The patient was assessed as Fitzpatrick phototype II; a dermoscopic photograph of a skin lesion; a female subject aged approximately 65: 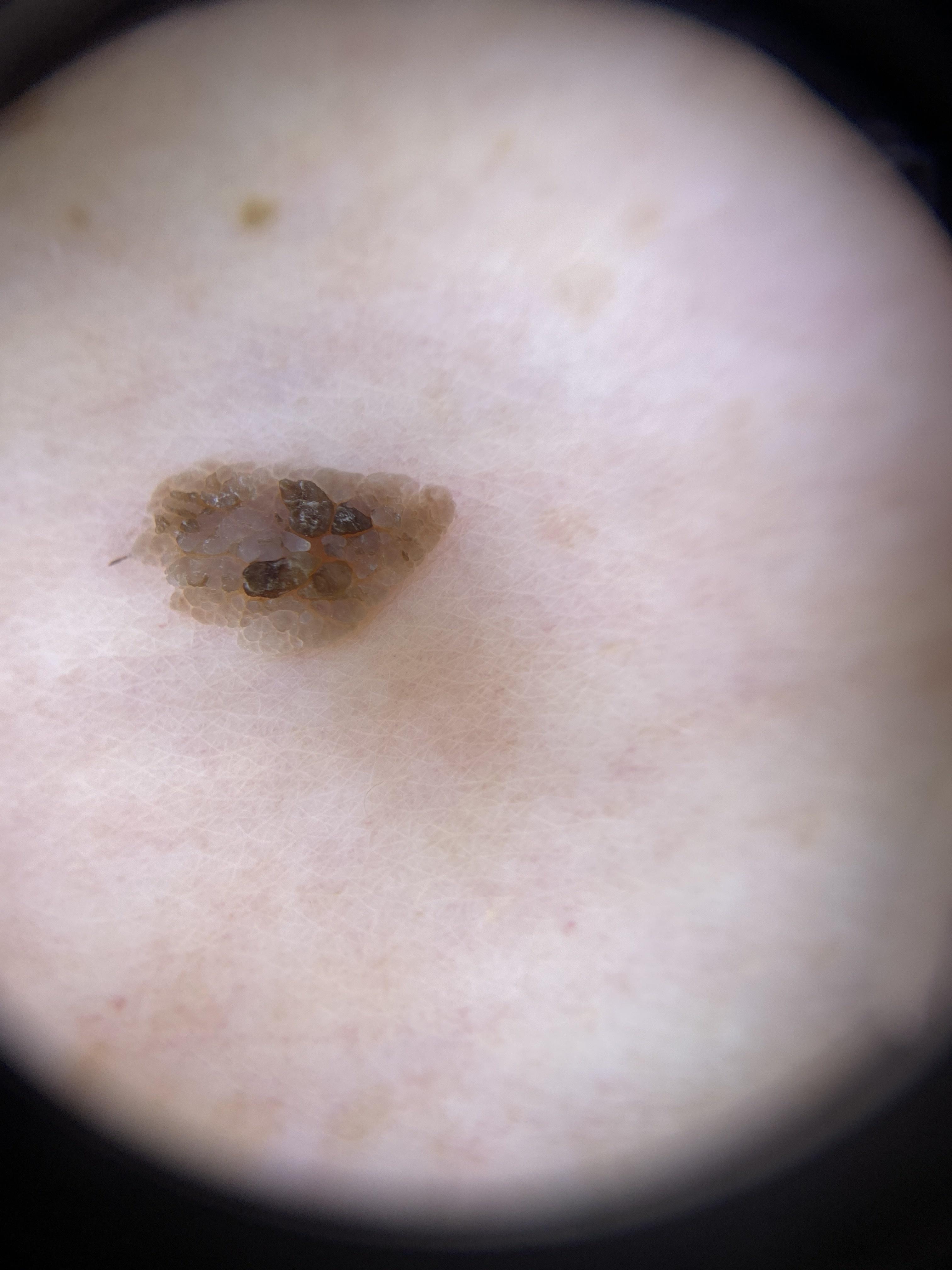Case summary: The lesion is on a lower extremity. Impression: Clinically diagnosed as a benign, epidermal lesion — a seborrheic keratosis.